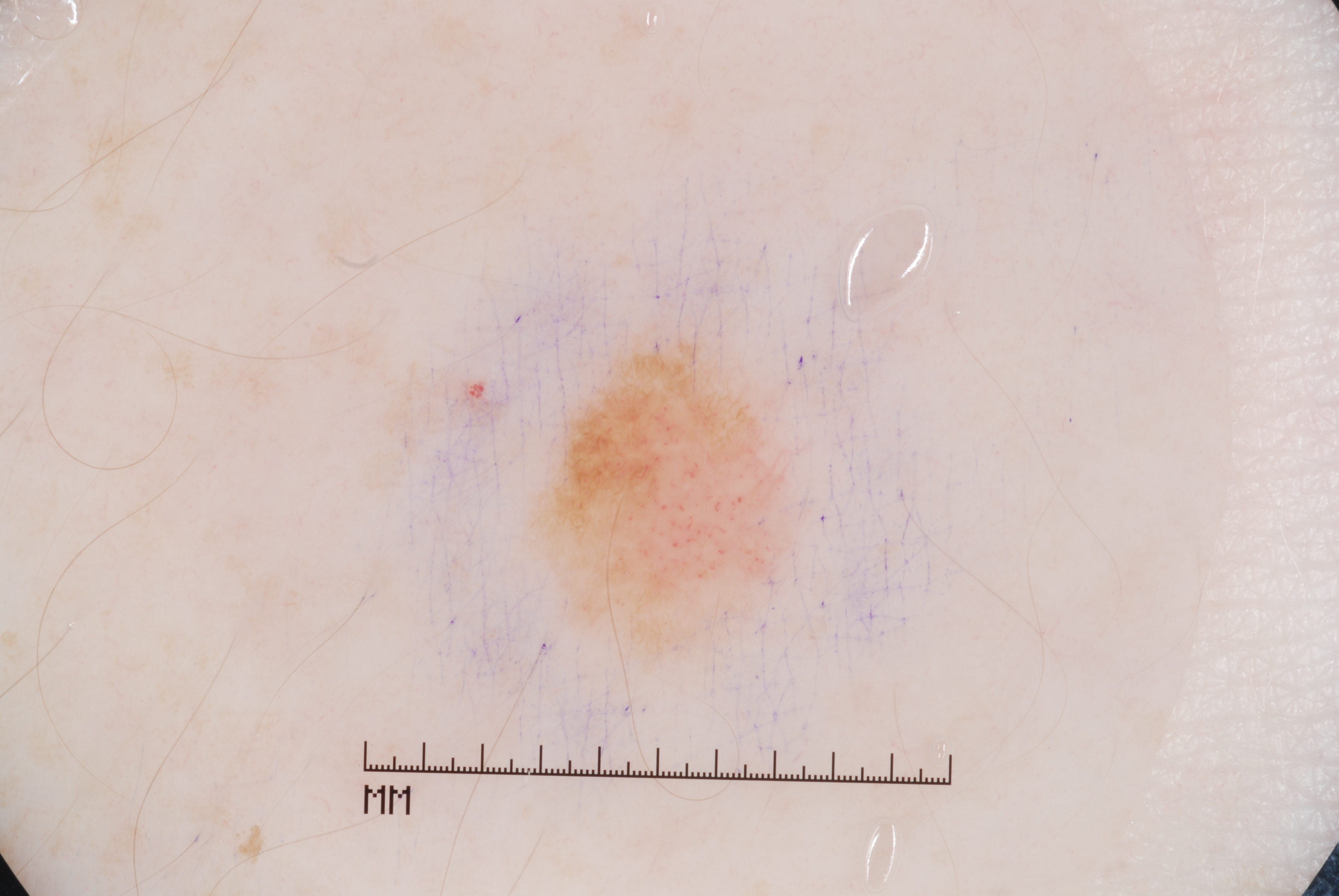Summary:
Dermoscopy of a skin lesion. A female subject, aged around 40. The lesion occupies roughly 5% of the field. With coordinates (x1, y1, x2, y2), the lesion spans [522,332,798,671]. Dermoscopic review identifies pigment network.
Impression:
Consistent with a melanocytic nevus, a benign lesion.